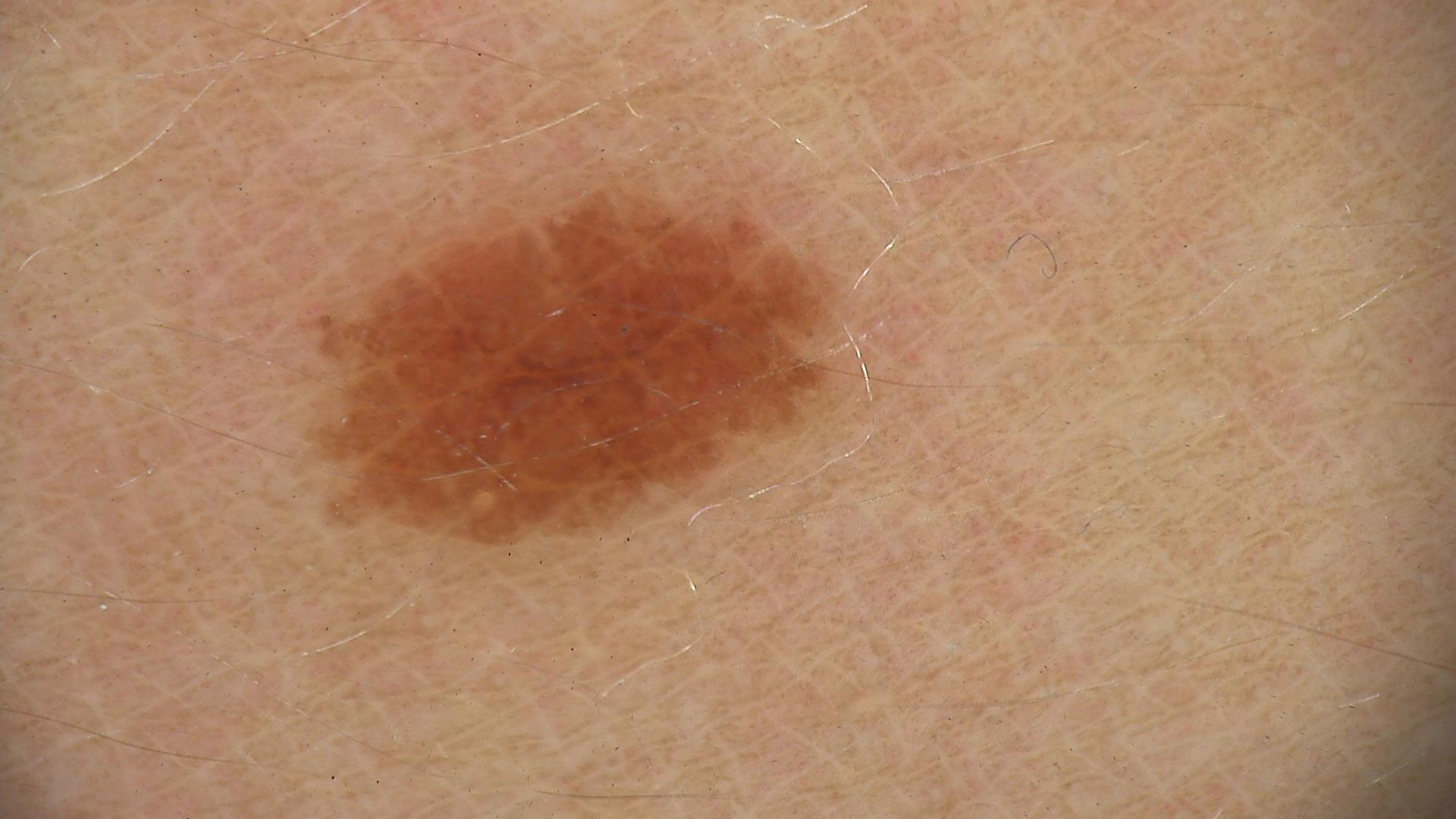diagnostic label = dysplastic junctional nevus (expert consensus).